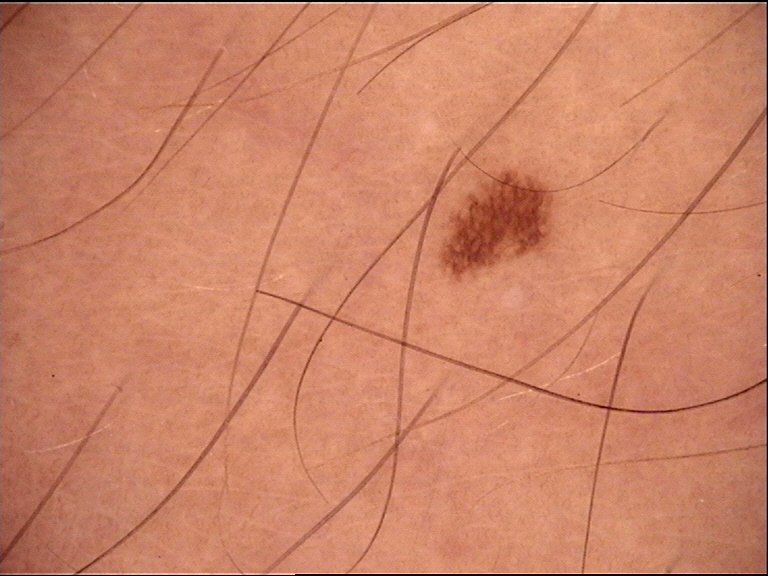This is a banal lesion. The diagnostic label was a junctional nevus.